The affected area is the arm; this is a close-up image; female subject, age 50–59 — 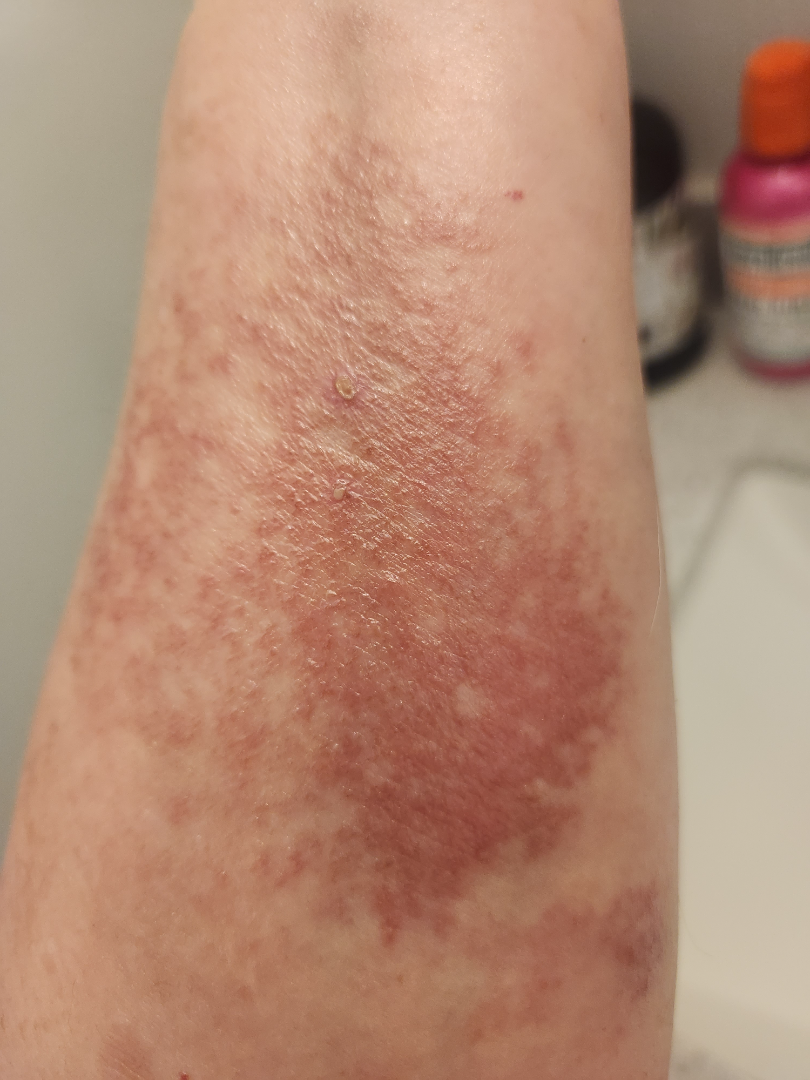Allergic Contact Dermatitis (primary); Tinea (possible); Eczema (possible).